Dermoscopy of a skin lesion.
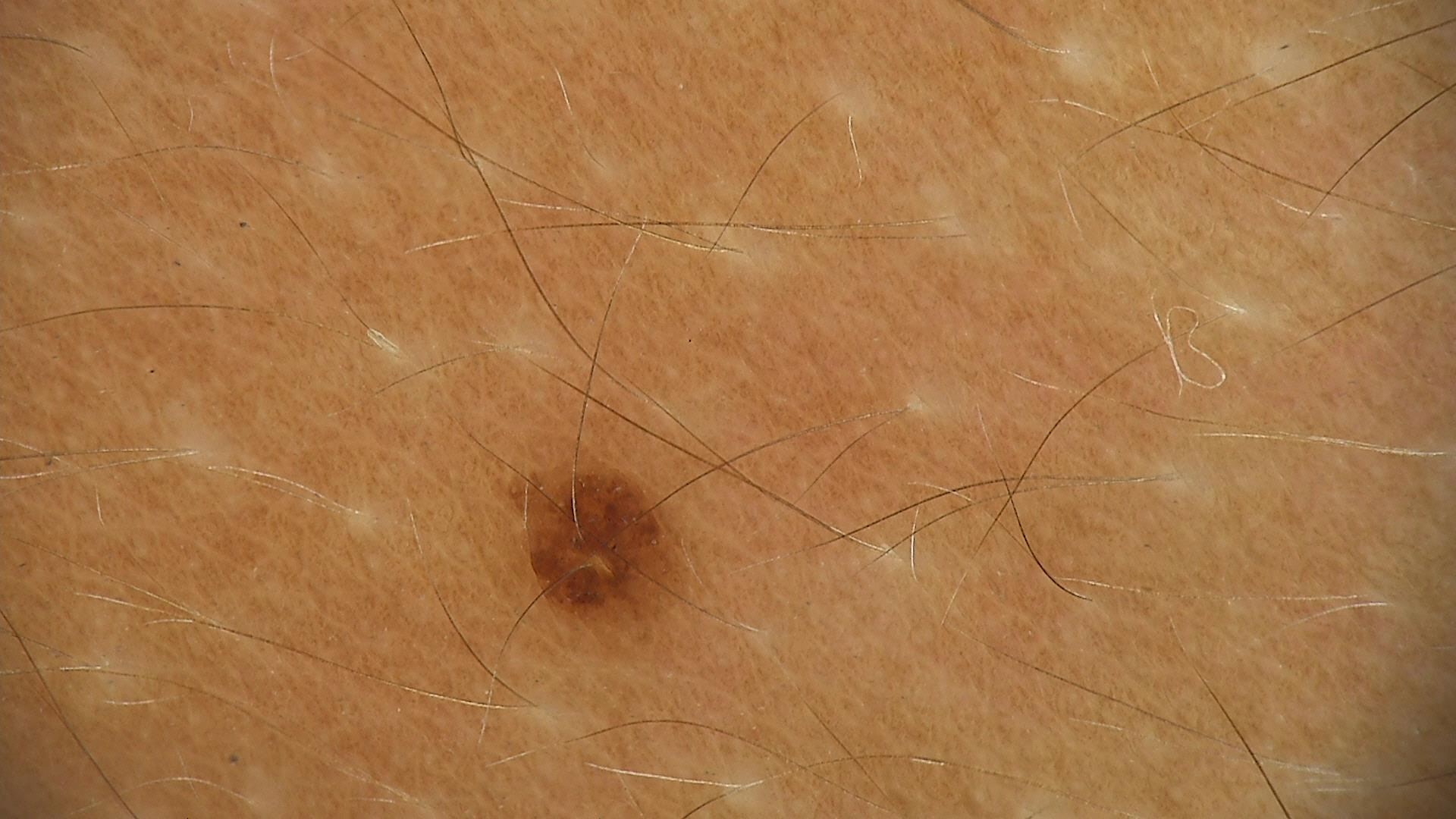assessment: dysplastic junctional nevus (expert consensus).